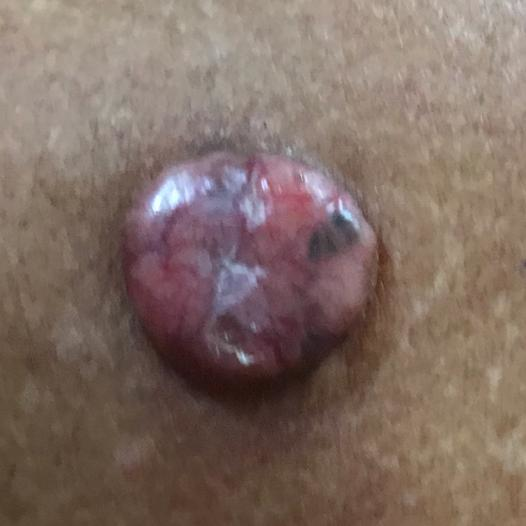FST: III
risk factors: alcohol use, tobacco use
modality: clinical photo
anatomic site: the back
pathology: basal cell carcinoma (biopsy-proven)